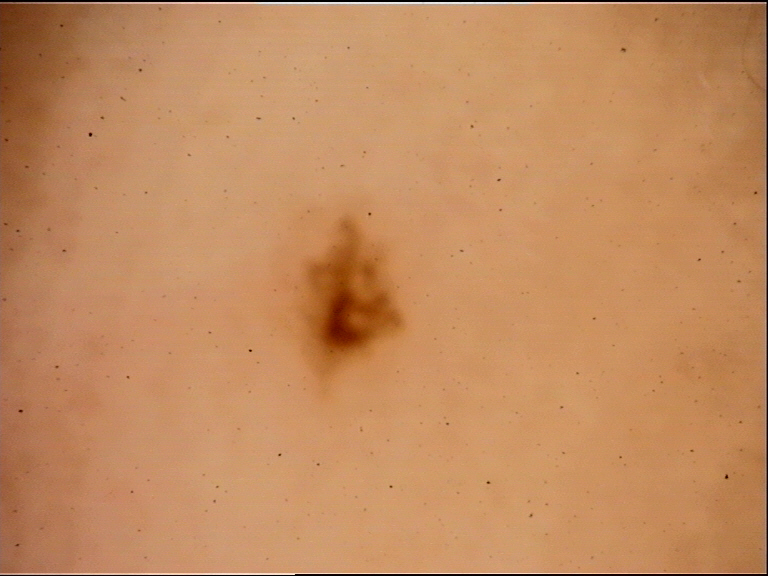{
  "diagnosis": {
    "name": "acral dysplastic junctional nevus",
    "code": "ajd",
    "malignancy": "benign",
    "super_class": "melanocytic",
    "confirmation": "expert consensus"
  }
}